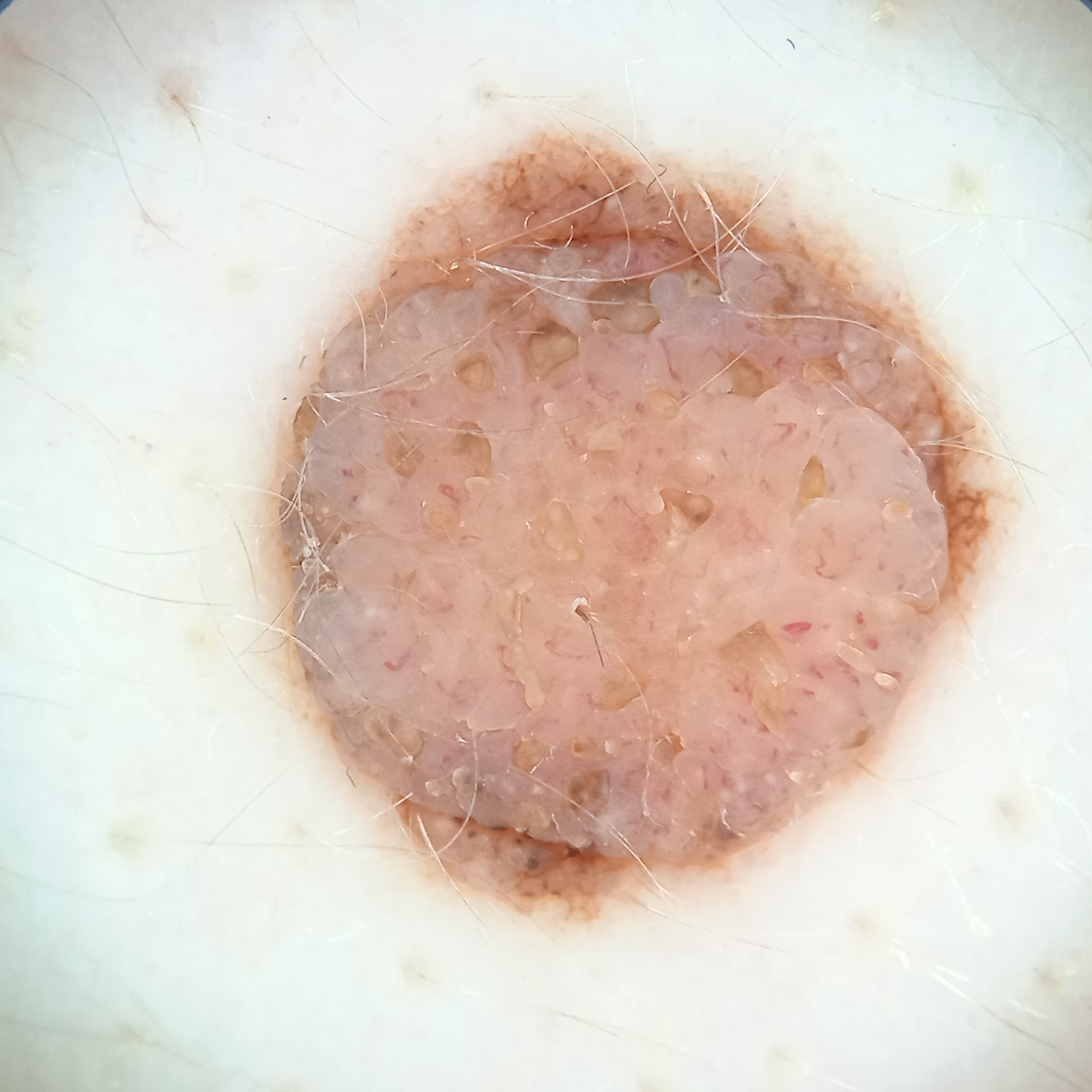The dermatologists' assessment was a melanocytic nevus.